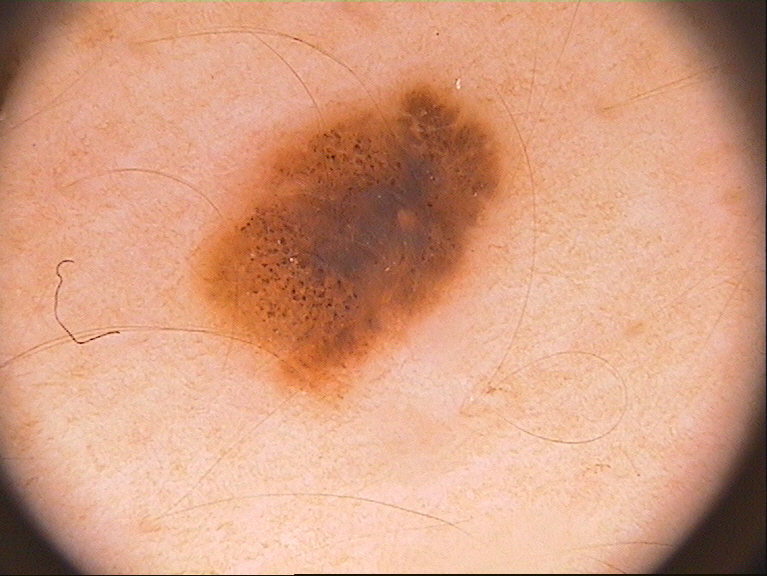image type: dermoscopic image | subject: female, aged around 30 | extent: ~17% of the field | dermoscopic findings: globules | bounding box: x1=181, y1=78, x2=517, y2=410 | diagnosis: a melanocytic nevus.